This is a close-up image; the patient notes darkening; the contributor is female; texture is reported as fluid-filled and rough or flaky; the leg and arm are involved — 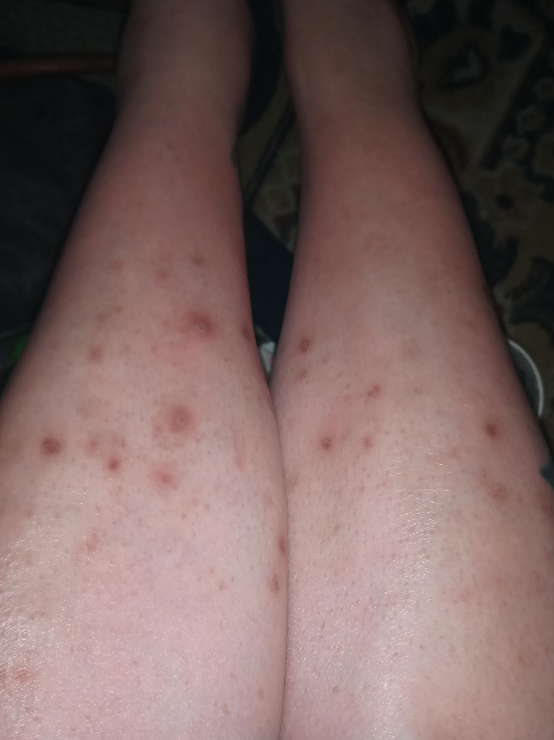differential diagnosis=reviewed remotely by three dermatologists: the leading consideration is Prurigo nodularis; possibly Folliculitis; also consider Insect Bite; less probable is Eczema; less likely is Vasculitis of the skin